A skin lesion imaged with a dermatoscope — 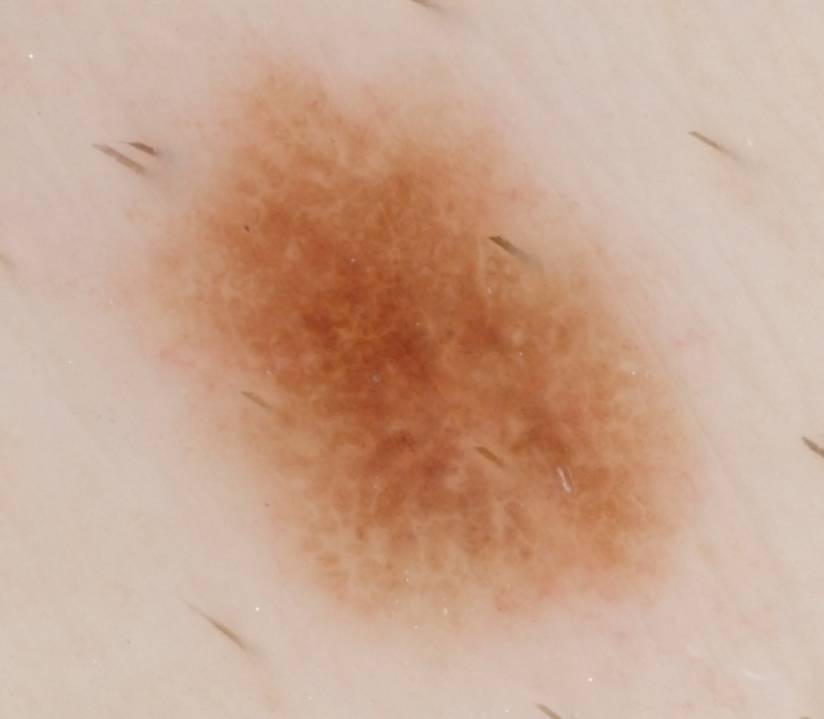Q: Lesion extent?
A: large
Q: Which dermoscopic features were noted?
A: negative network and globules
Q: Where is the lesion in the image?
A: left=146, top=70, right=674, bottom=620
Q: What did the assessment conclude?
A: a melanocytic nevus